The photograph was taken at an angle. The patient is a female aged 18–29. Located on the back of the torso, arm, front of the torso, leg and head or neck: 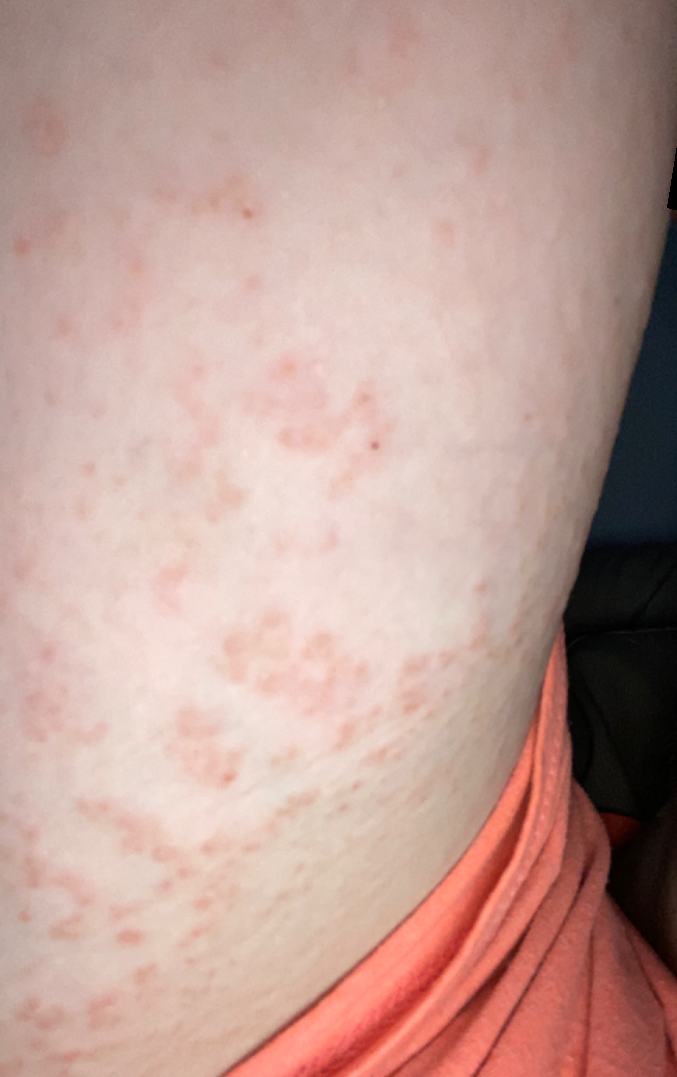Q: What conditions are considered?
A: most likely Allergic Contact Dermatitis; also raised was Keratosis pilaris; with consideration of Eczema